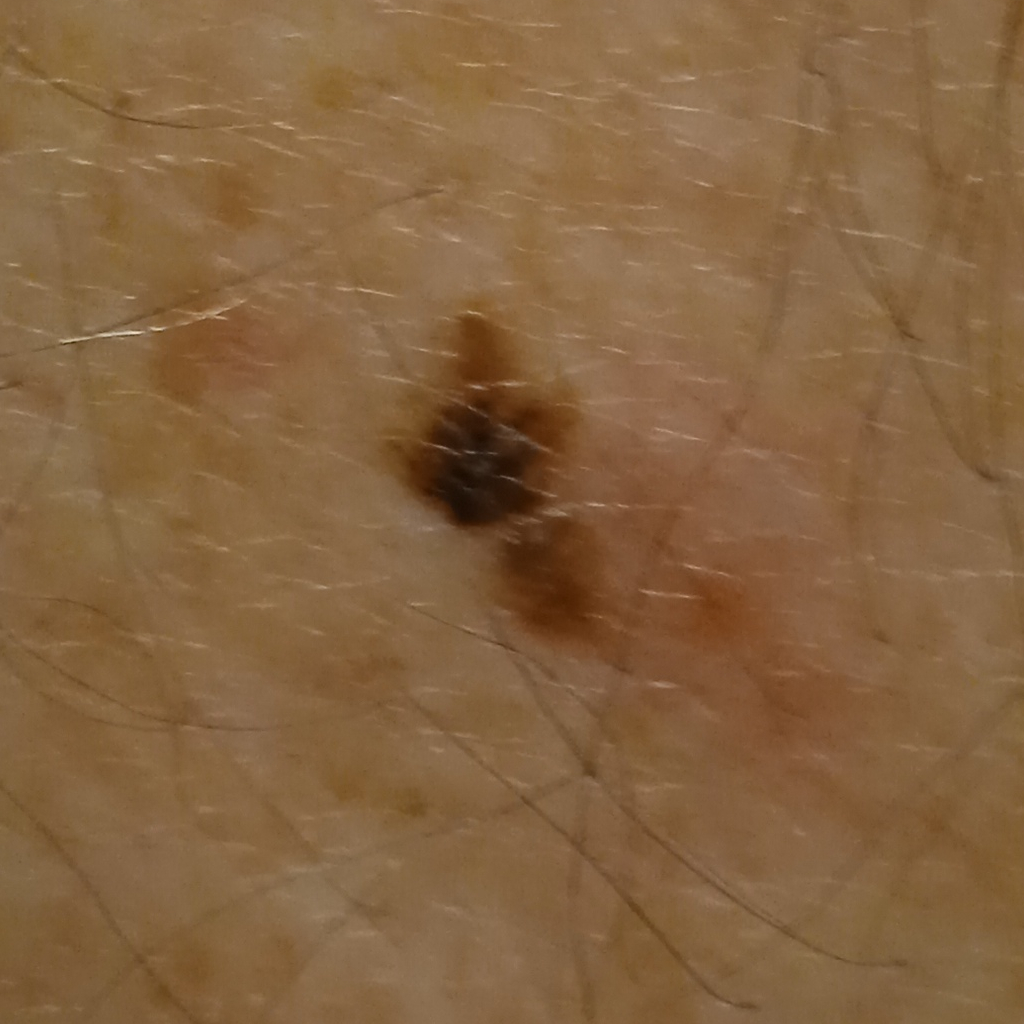The patient says their skin reddens with sun exposure. The patient describes having few moles overall. Collected as part of a research study, without a referral diagnosis. The lesion is located on the back. The lesion was assessed as a seborrheic keratosis.